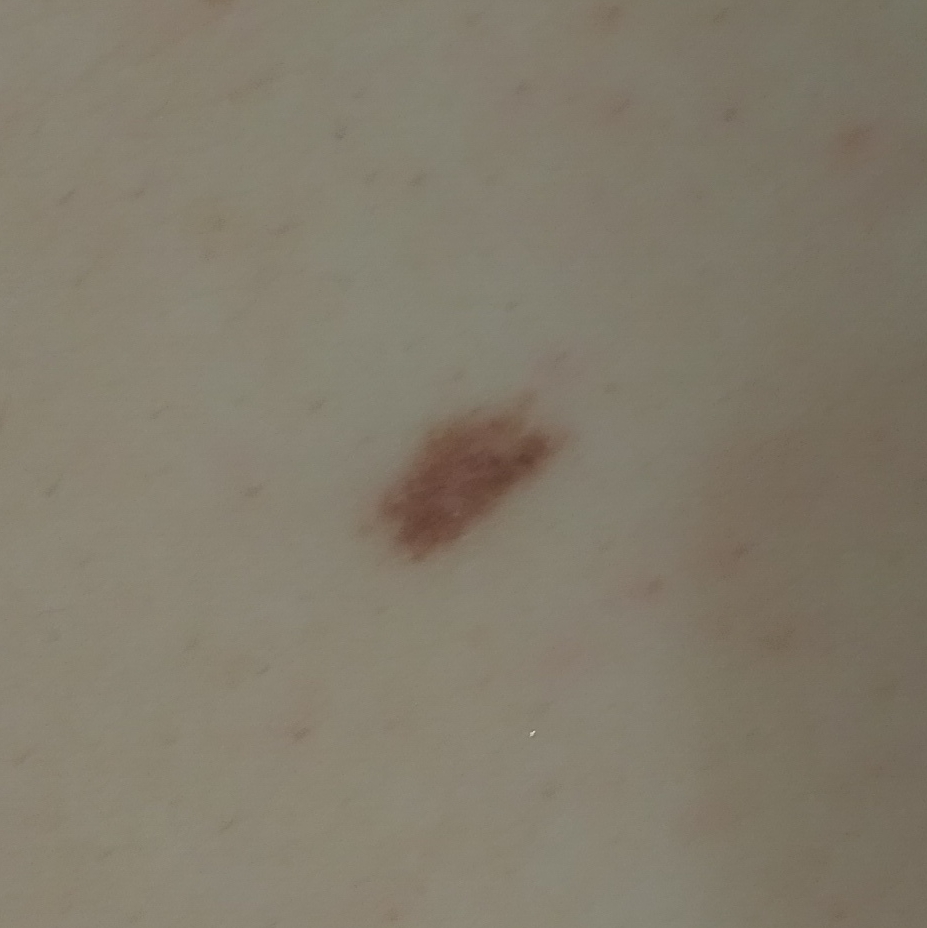A subject in their late 20s. A clinical photograph showing a skin lesion. The lesion involves the abdomen. No symptoms reported. Consistent with a nevus.